The photo was captured at a distance. Skin tone: Fitzpatrick phototype I.
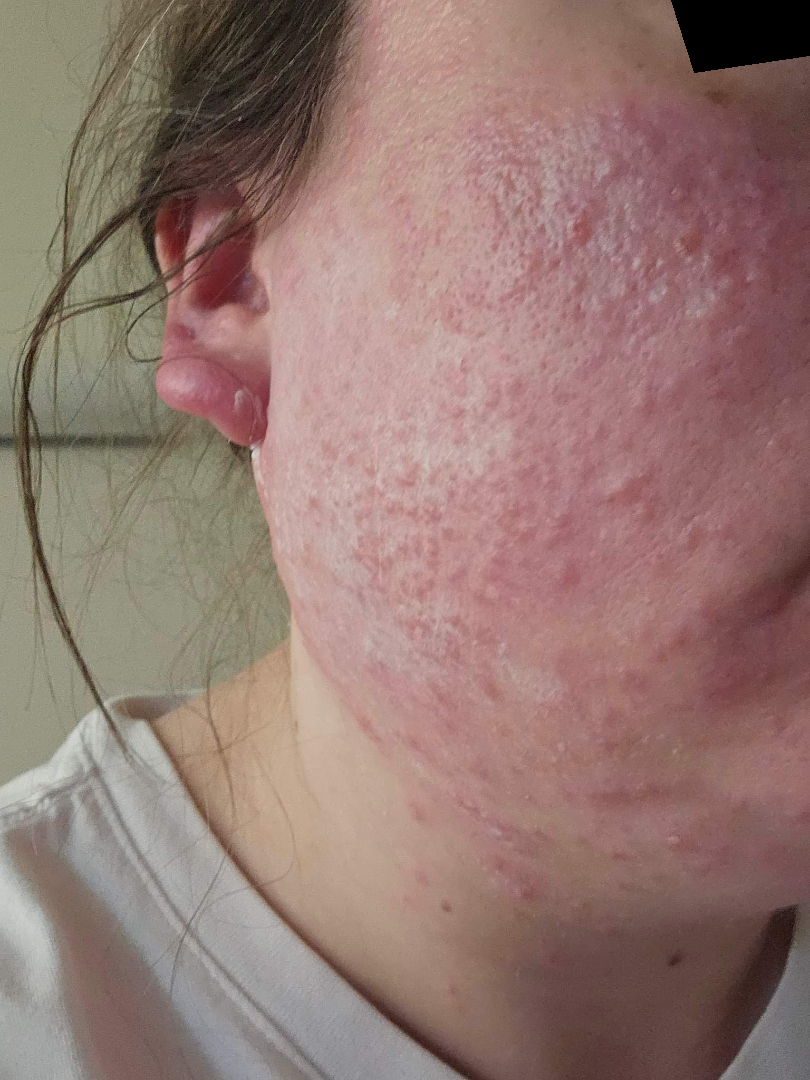Findings:
On remote review of the image: the primary impression is Rosacea; possibly Acne.